No constitutional symptoms were reported · located on the front of the torso and back of the torso · an image taken at an angle · present for less than one week · reported lesion symptoms include burning, enlargement and bothersome appearance · the patient considered this a rash · texture is reported as flat and raised or bumpy: 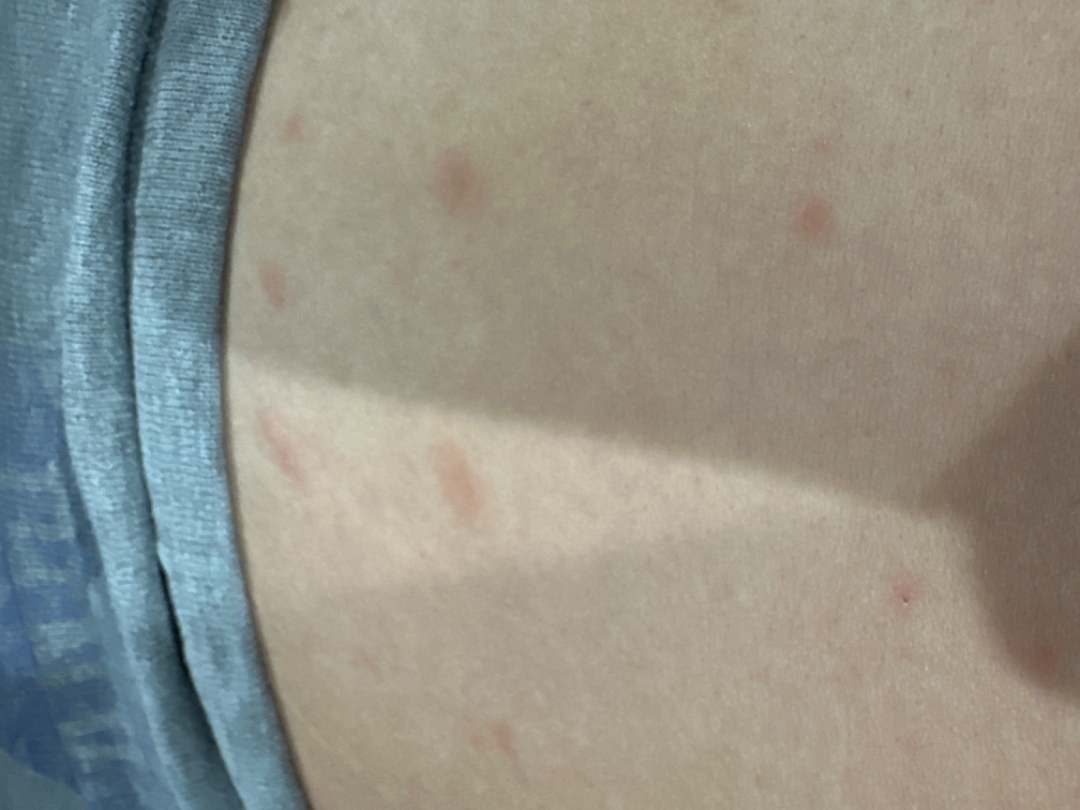- assessment — the primary impression is Pityriasis rosea; possibly Eczema; also consider Syphilis